Skin tone: Fitzpatrick skin type III. The lesion is described as rough or flaky. The patient indicates itching and bothersome appearance. The patient indicates the condition has been present for about one day. Self-categorized by the patient as a rash. A close-up photograph. Located on the head or neck. Male patient, age 18–29 — 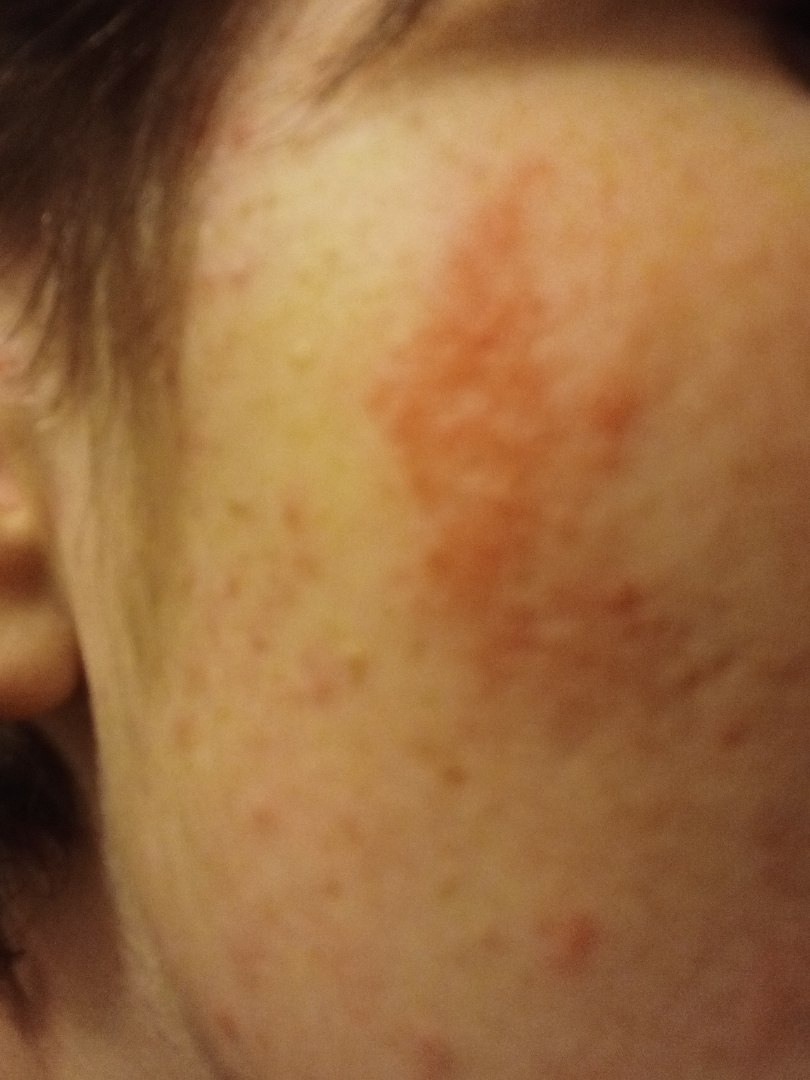{"differential": {"leading": ["Acne"], "considered": ["Irritant Contact Dermatitis"]}}